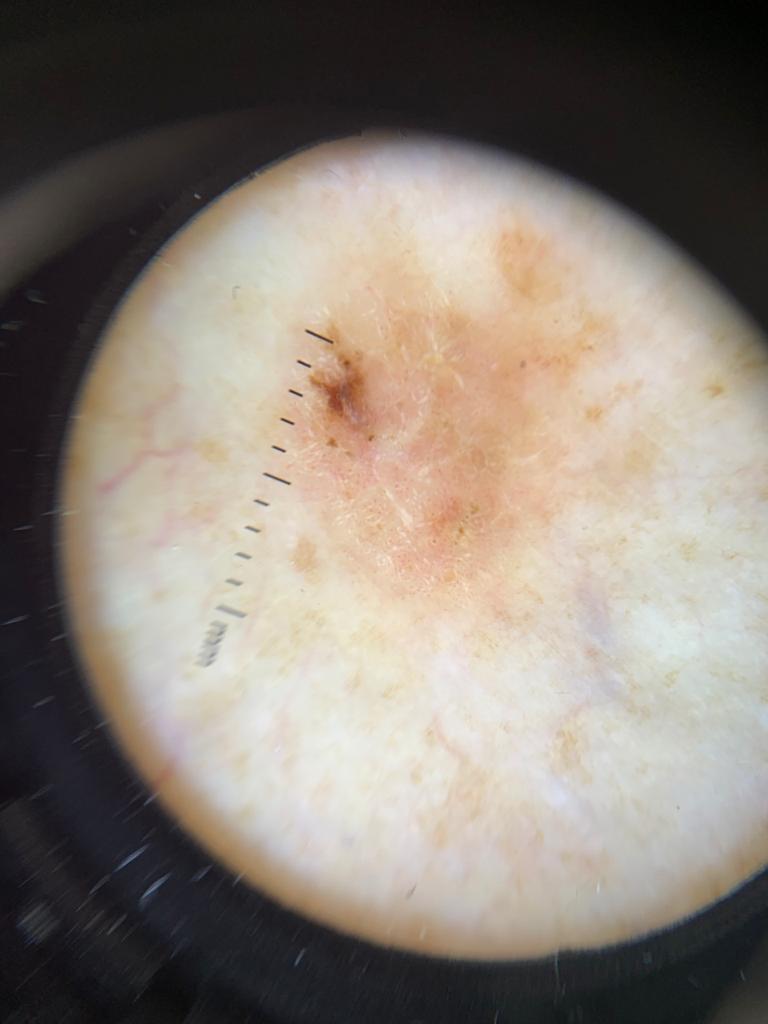Per the chart, a prior melanoma but no melanoma in first-degree relatives. Contact-polarized dermoscopy of a skin lesion. A female patient about 60 years old. The lesion was found on a lower extremity. Histopathological examination showed a malignant lesion — a melanoma.